A close-up photograph · the subject is a female aged 60–69 — 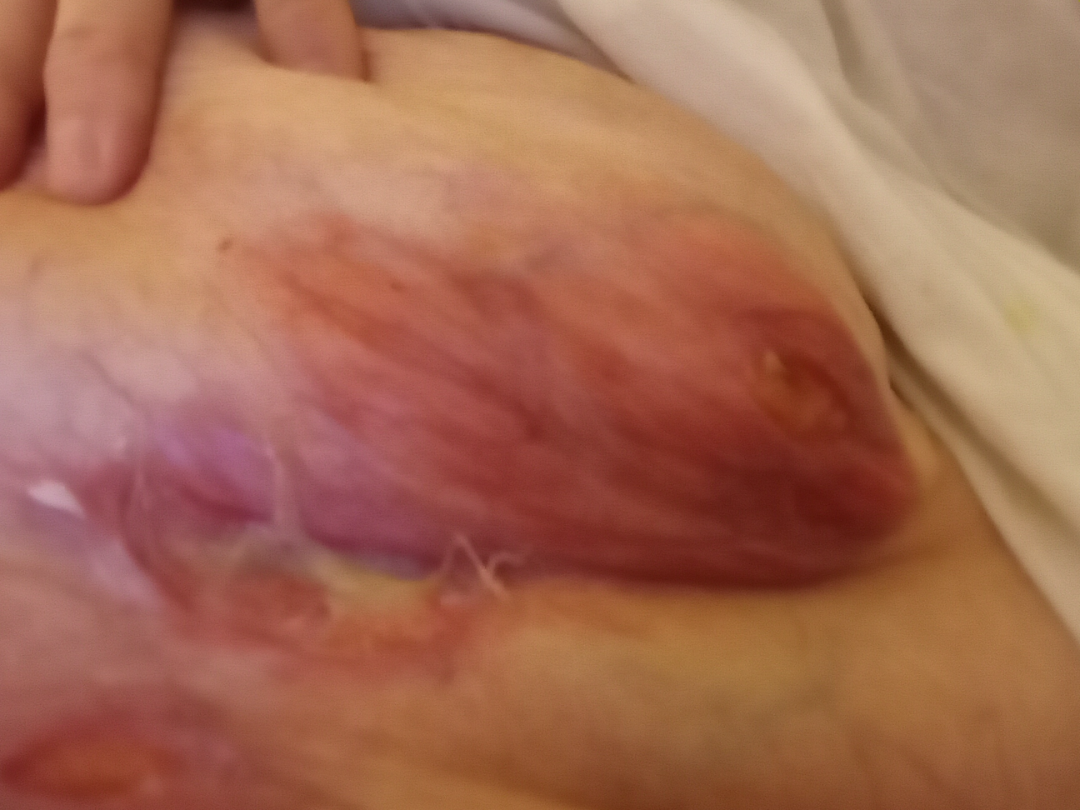The condition could not be reliably identified from the image.
The patient indicates associated fatigue.
The patient indicates the lesion is fluid-filled.
The patient indicates the condition has been present for more than one year.
Reported lesion symptoms include burning, enlargement, bleeding, itching and pain.
Skin tone: self-reported FST II.